The patient was assessed as Fitzpatrick skin type IV. A clinical photograph of a skin lesion. History notes prior malignancy (patient or family) and pesticide exposure. A male patient in their 30s — 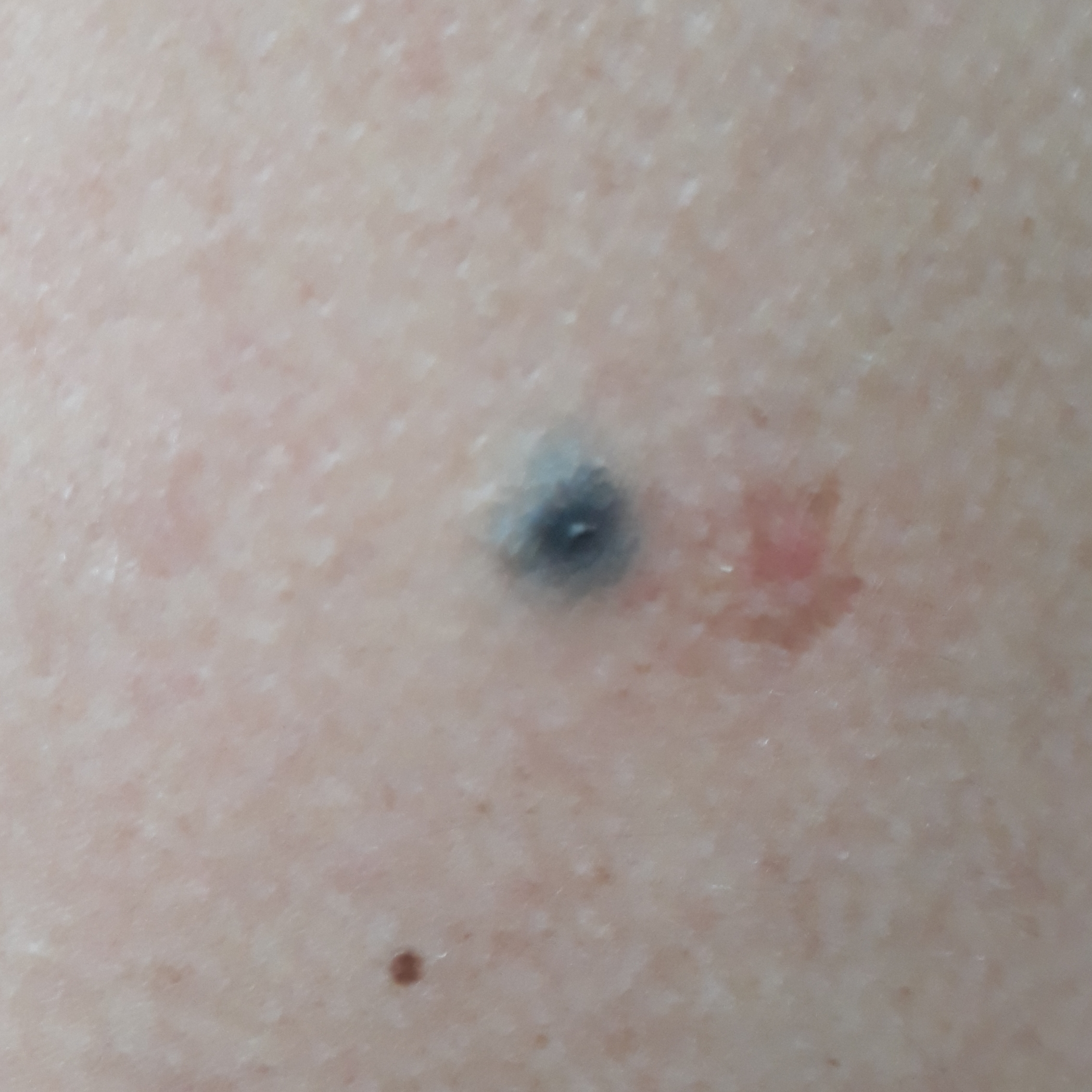lesion_location: the chest
lesion_size:
  diameter_1_mm: 6.0
  diameter_2_mm: 5.0
symptoms:
  present:
    - change in appearance
    - growth
    - elevation
  absent:
    - pain
diagnosis:
  name: nevus
  code: NEV
  malignancy: benign
  confirmation: histopathology